The contributor is a female aged 30–39. Close-up view. The lesion involves the top or side of the foot:
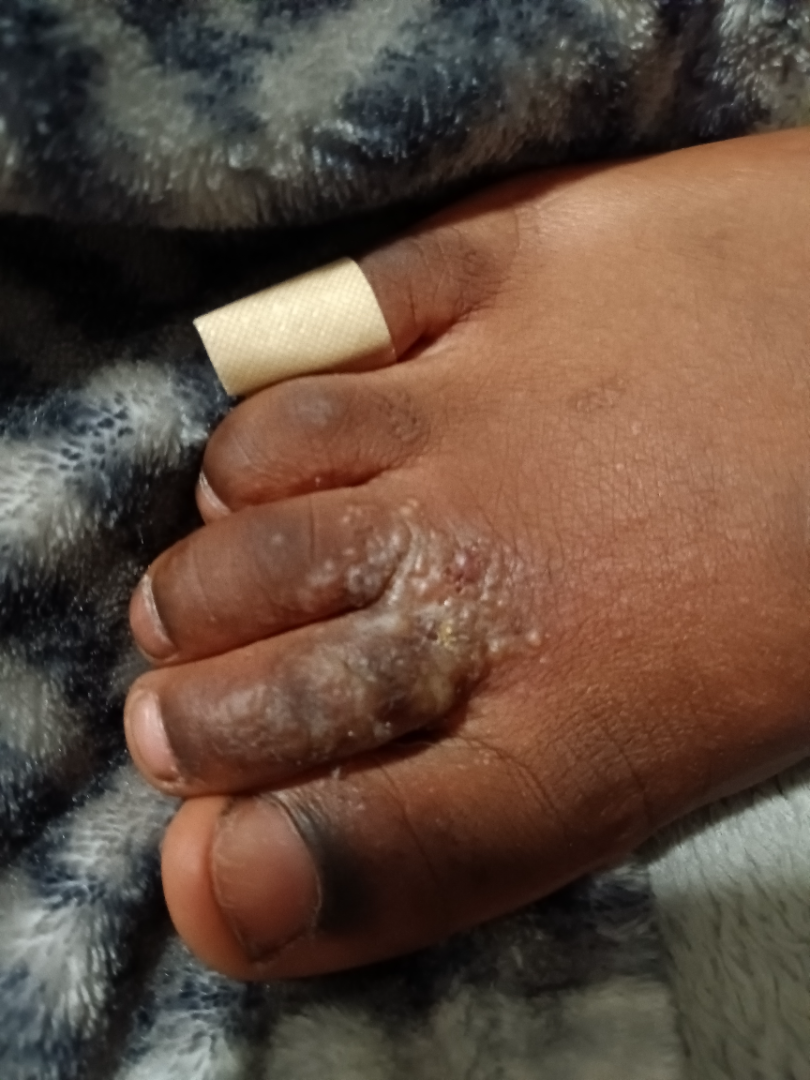Reported lesion symptoms include itching and bothersome appearance. Reported duration is less than one week. Fitzpatrick skin type V. On remote review of the image: the differential, in no particular order, includes Tinea and Eczema; possibly Skin and soft tissue atypical mycobacterial infection; less likely is Allergic Contact Dermatitis.